The lesion involves the leg. An image taken at a distance — 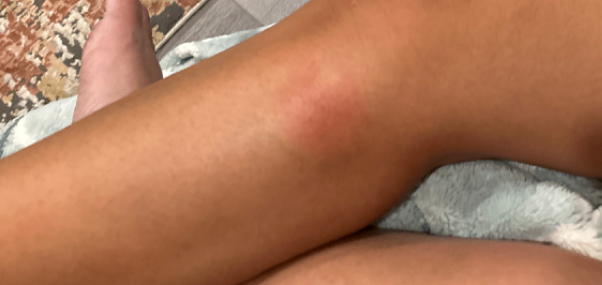dermatologist impression — Cellulitis and Insect Bite were each considered, in no particular order; less likely is Acute dermatitis, NOS; lower on the differential is Erythema nodosum; a remote consideration is Drug Rash